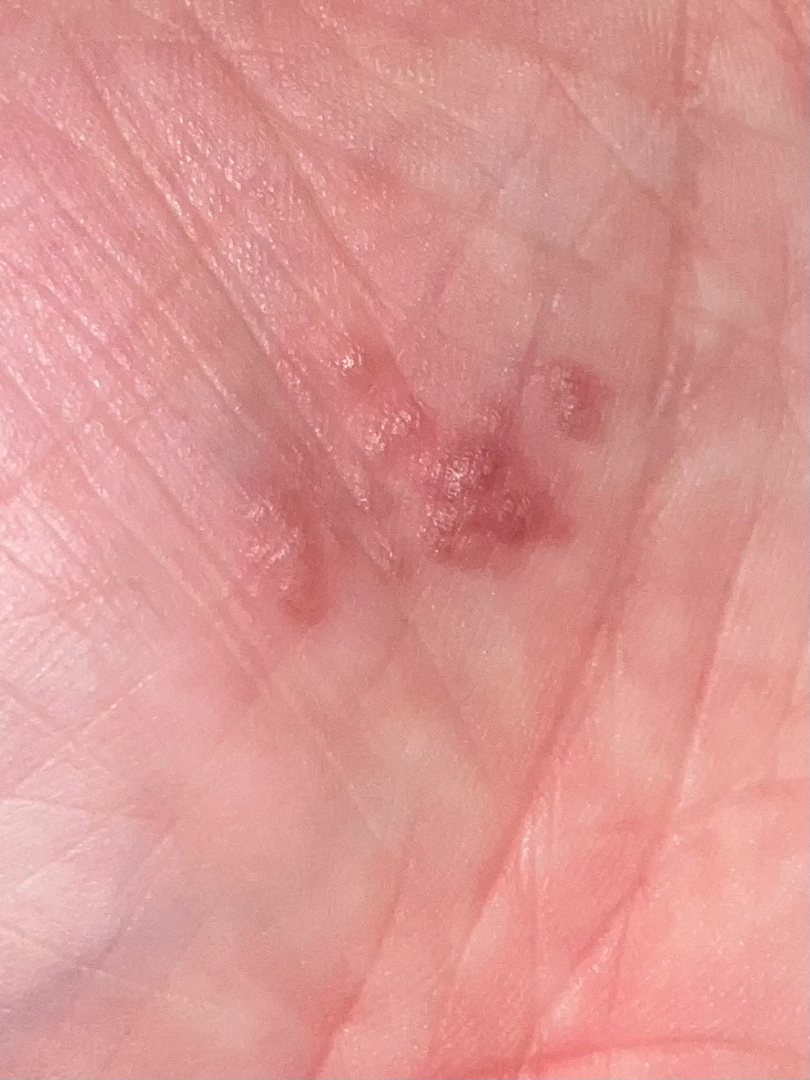The patient notes the condition has been present for less than one week.
Close-up view.
The lesion involves the palm.
Male patient, age 40–49.
The lesion is associated with burning and bothersome appearance.
The patient also reports shortness of breath.
The patient described the issue as a rash.
Texture is reported as fluid-filled and raised or bumpy.
Most consistent with Eczema.